A female patient in their 70s · contact-polarized dermoscopy of a skin lesion:
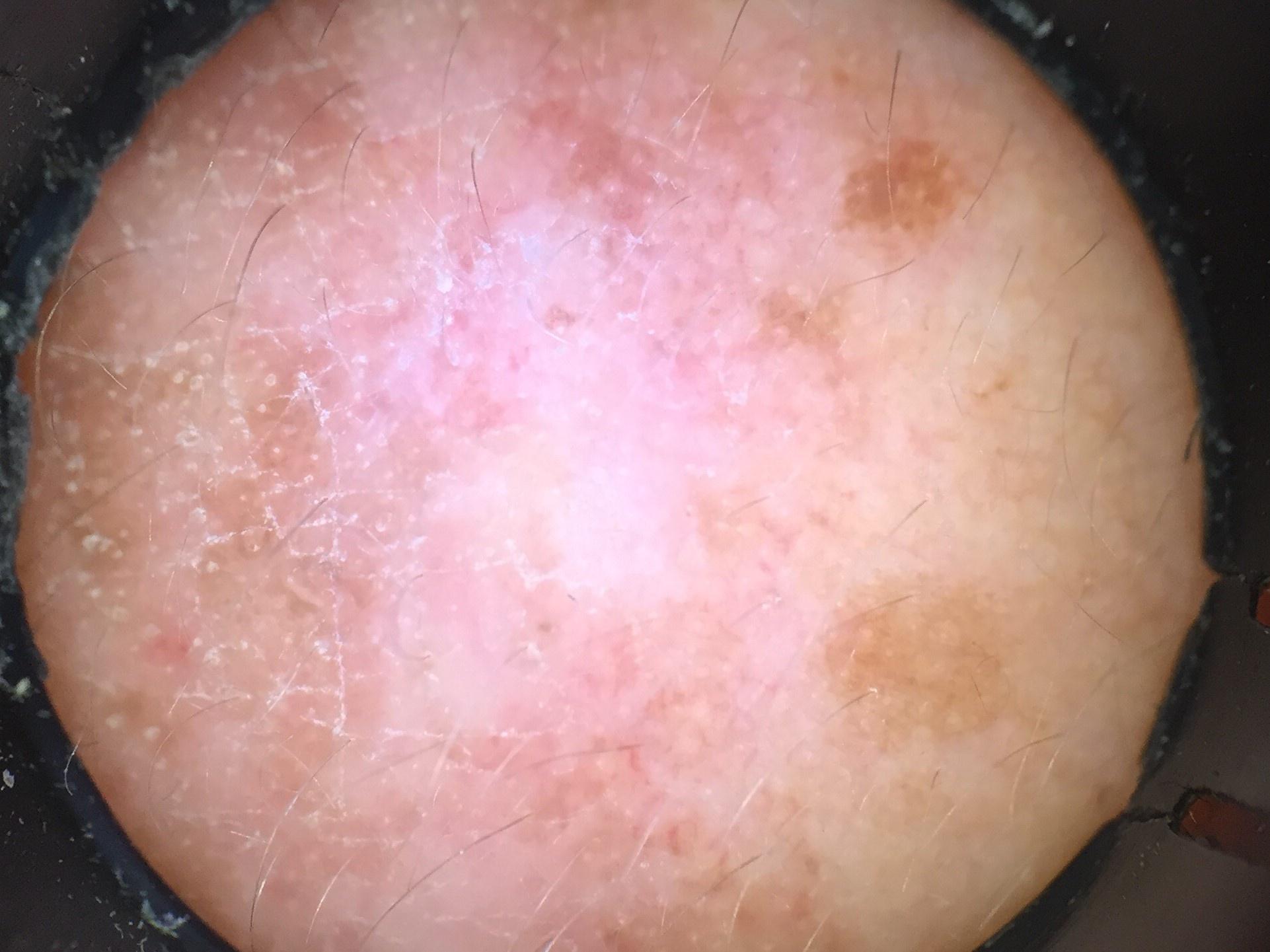<skin_lesion>
<lesion_location>
<region>the head or neck</region>
</lesion_location>
<diagnosis>
<name>Squamous cell carcinoma</name>
<malignancy>malignant</malignancy>
<confirmation>histopathology</confirmation>
<lineage>epidermal</lineage>
</diagnosis>
</skin_lesion>